A clinical photograph of a skin lesion; few moles overall by the patient's own estimate; the patient says their skin reddens with sun exposure; a female subject 39 years old:
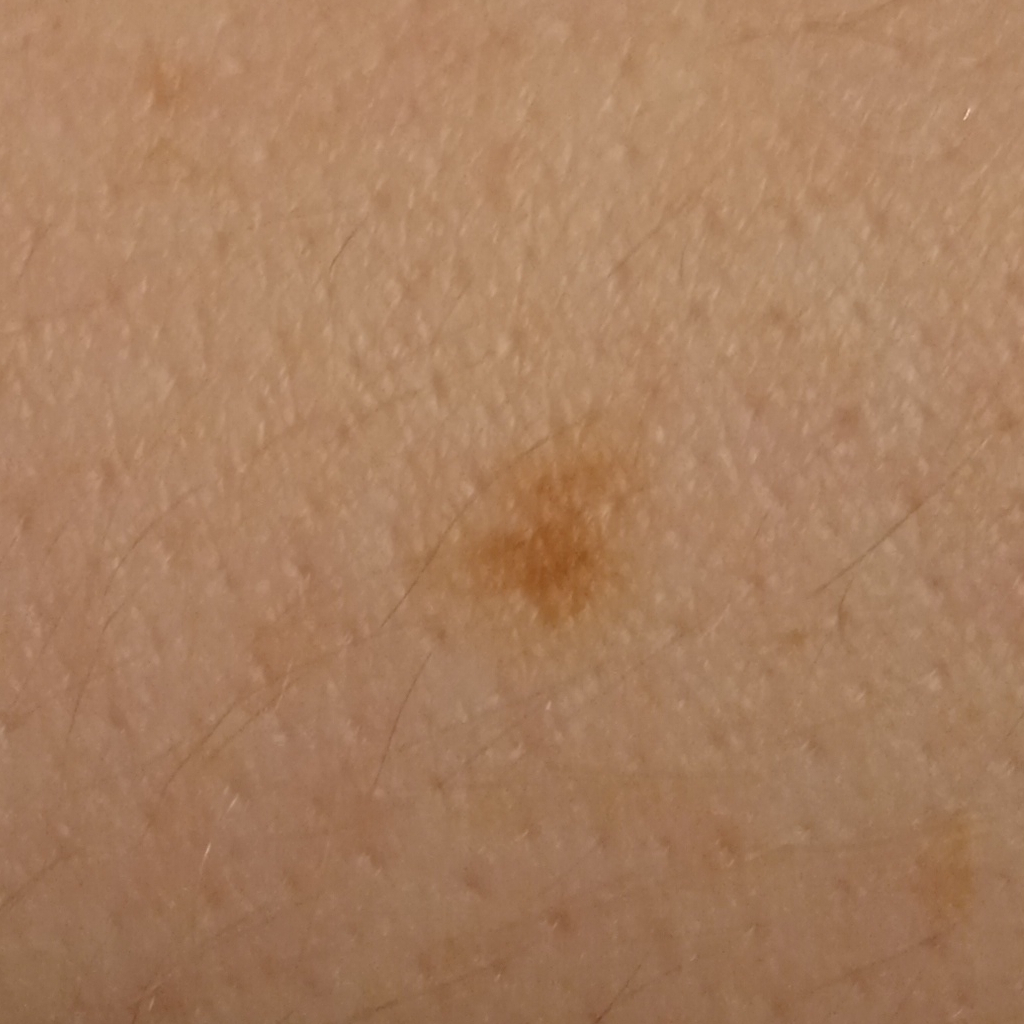Clinical context:
The lesion is located on an arm. Measuring roughly 5.1 mm.
Conclusion:
The lesion was assessed as a melanocytic nevus.